Fitzpatrick skin type I; human graders estimated 2 on the Monk skin tone scale · this is a close-up image: 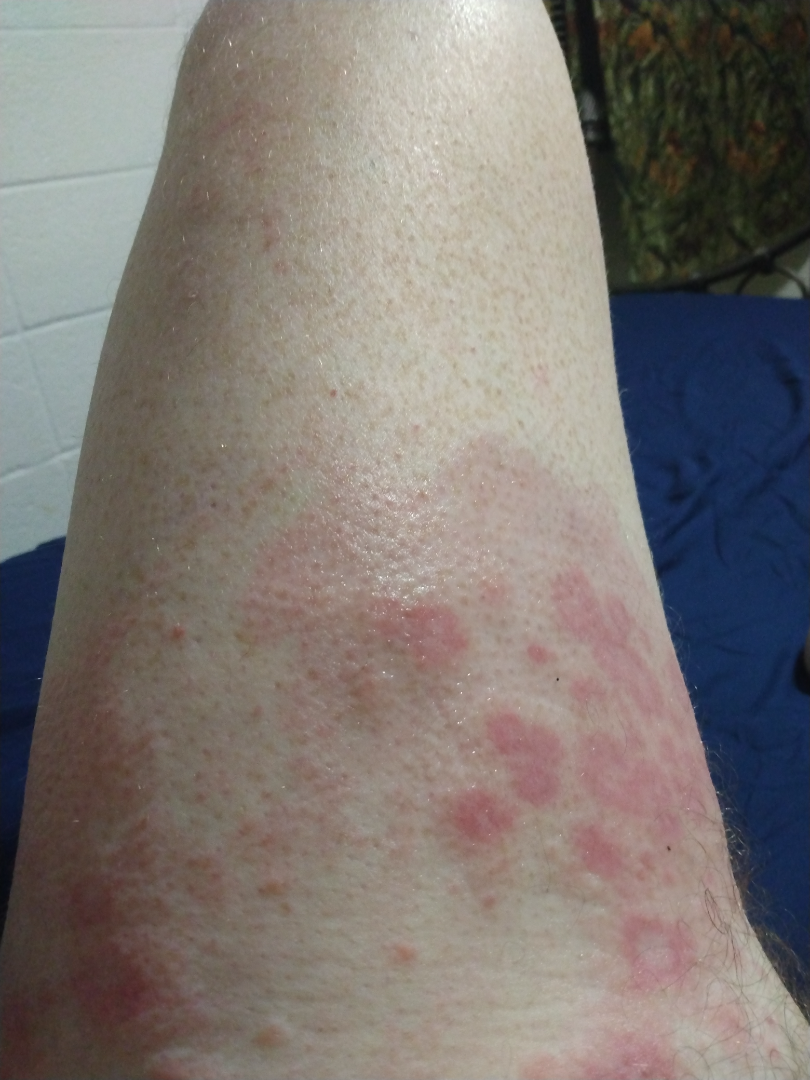Most consistent with Urticaria; also consider Erythema multiforme; possibly Allergic Contact Dermatitis.